Skin tone: Fitzpatrick III; lay reviewers estimated Monk Skin Tone 2 or 3 (two reviewer pools). This image was taken at an angle. The arm is involved. Self-categorized by the patient as a rash. The contributor reports the condition has been present for about one day. Reported lesion symptoms include itching. The lesion is described as raised or bumpy.
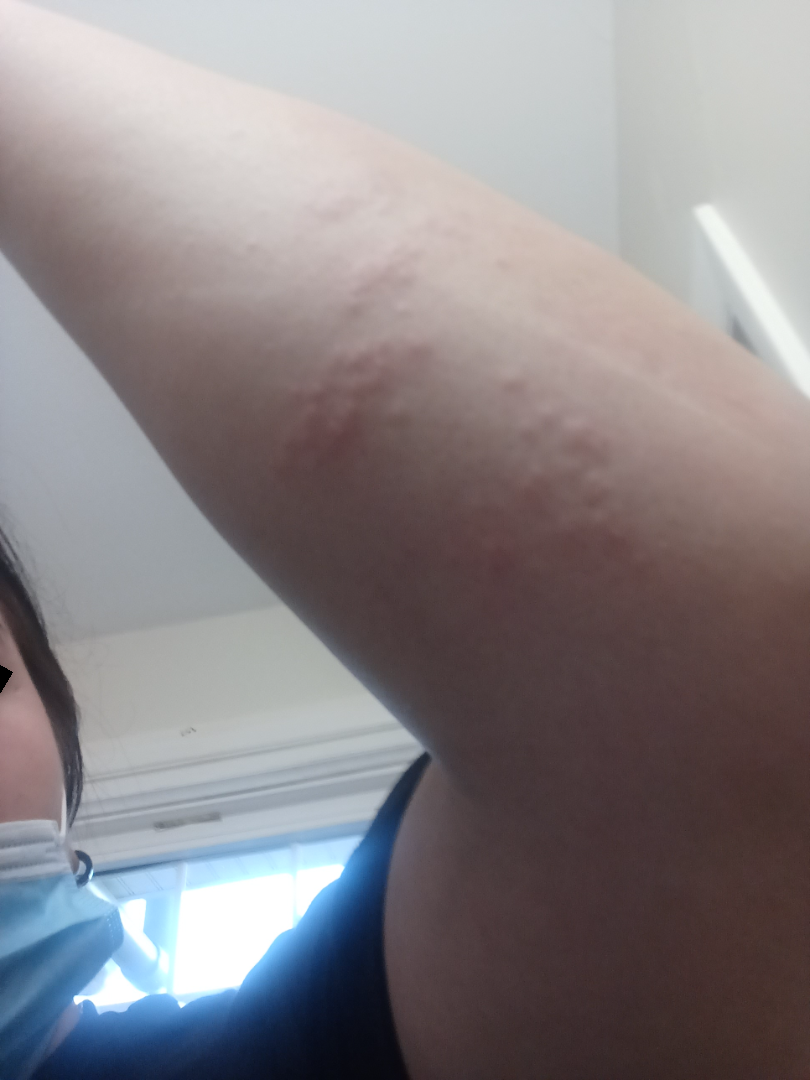| key | value |
|---|---|
| assessment | ungradable on photographic review |